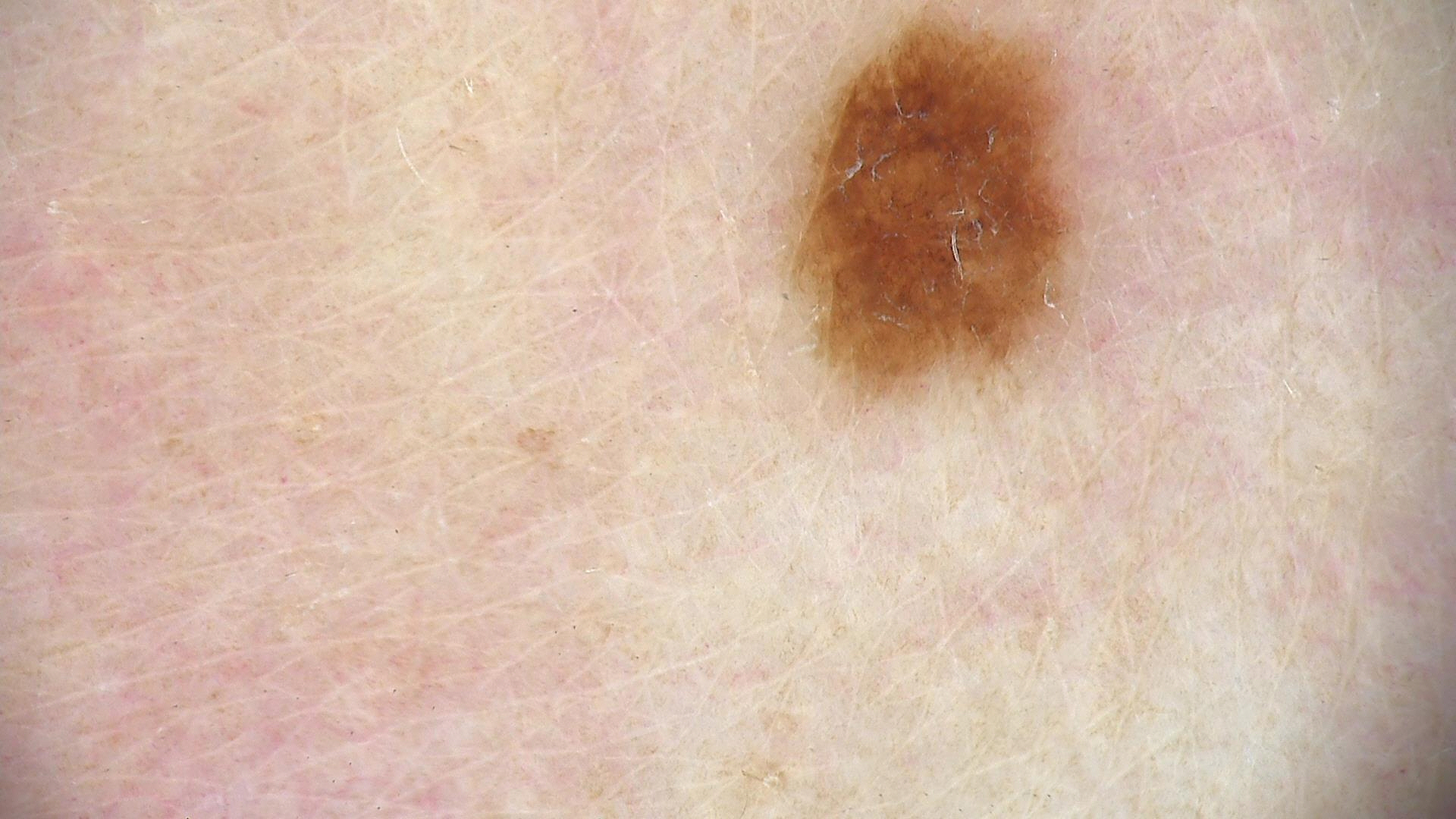* modality — dermatoscopy
* diagnosis — junctional nevus (expert consensus)